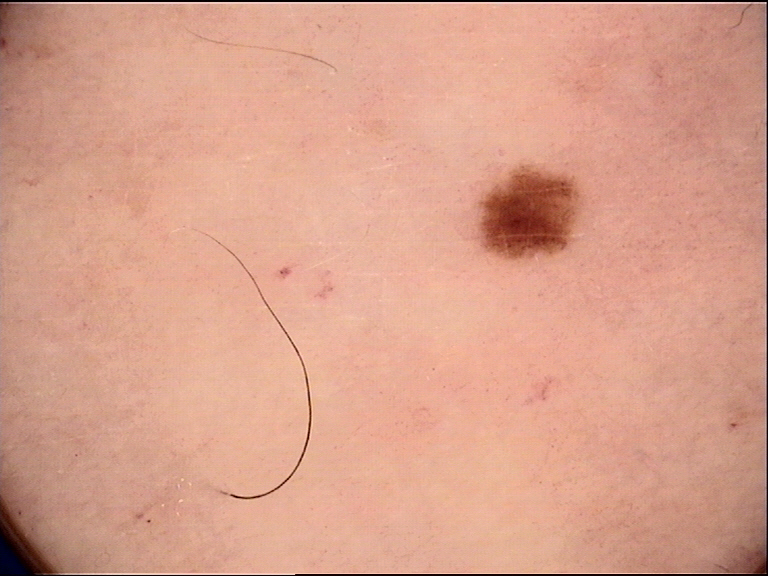Conclusion:
Diagnosed as a dysplastic junctional nevus.